A dermatoscopic image of a skin lesion: 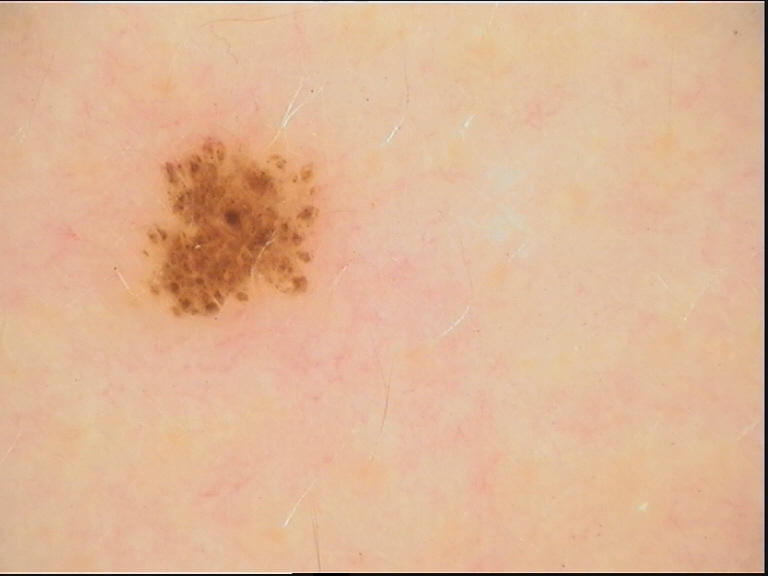Conclusion: Classified as a dysplastic junctional nevus.